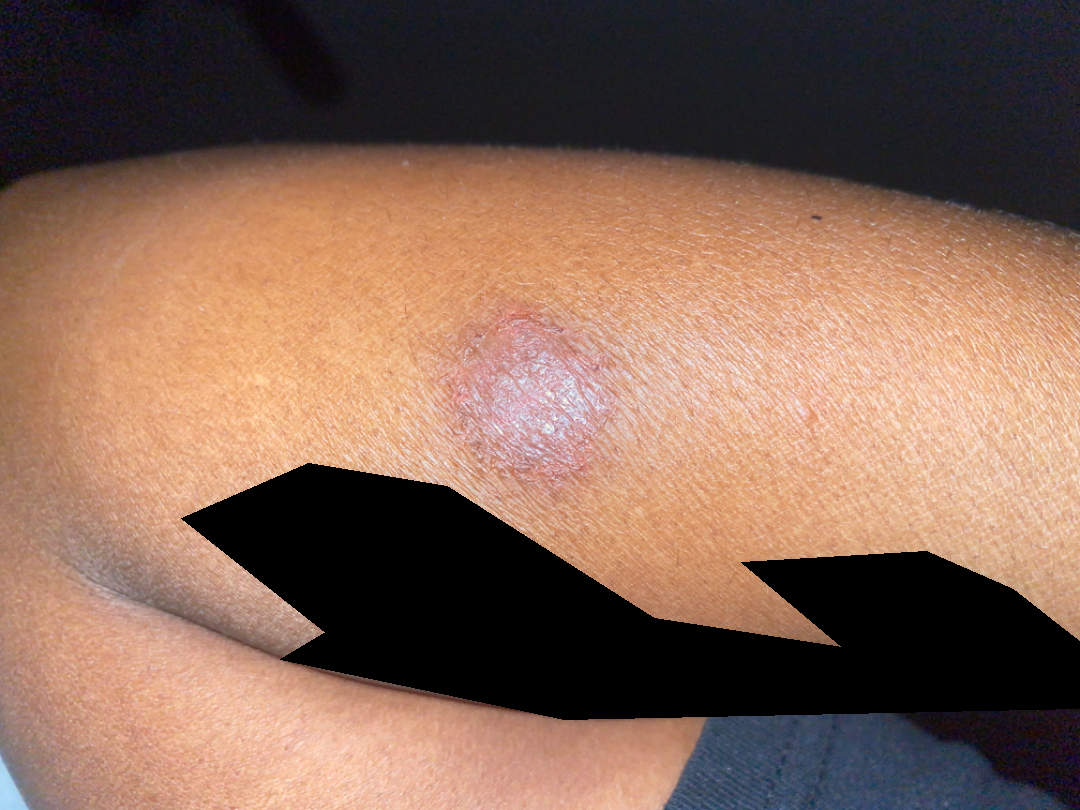| field | value |
|---|---|
| assessment | ungradable on photographic review |
| image framing | at an angle |